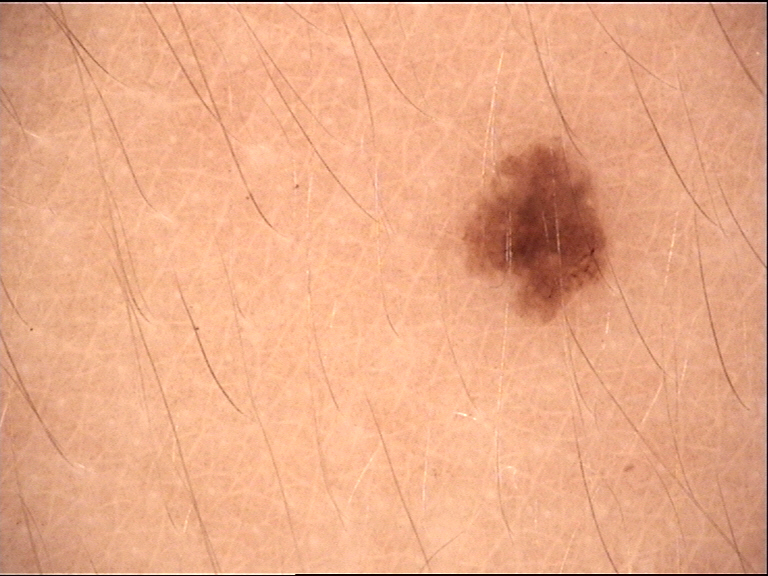Findings:
• imaging — dermatoscopy
• diagnosis — junctional nevus (expert consensus)